Fitzpatrick phototype II; lay reviewers estimated Monk skin tone scale 4 (US pool) or 2 (India pool). No associated systemic symptoms reported. The lesion is described as raised or bumpy. The patient considered this skin that appeared healthy to them. The patient notes itching. The photograph is a close-up of the affected area. The affected area is the arm. Reported duration is about one day.
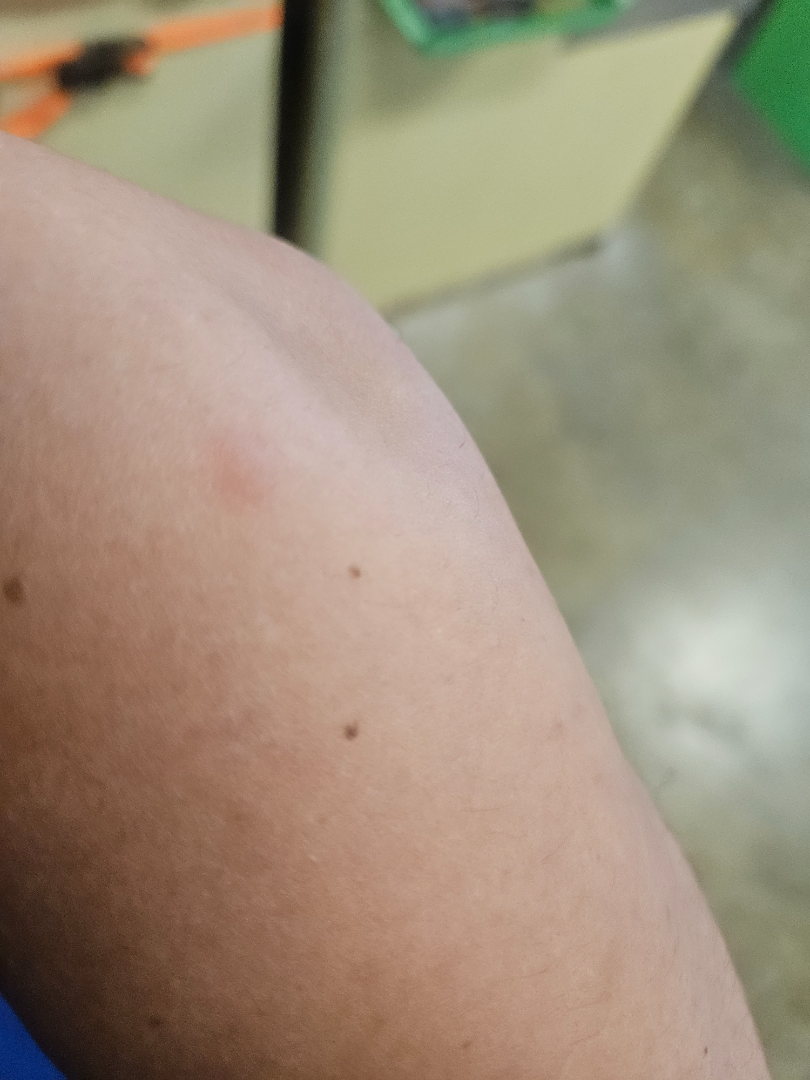clinical impression = favoring Insect Bite; also on the differential is Urticaria